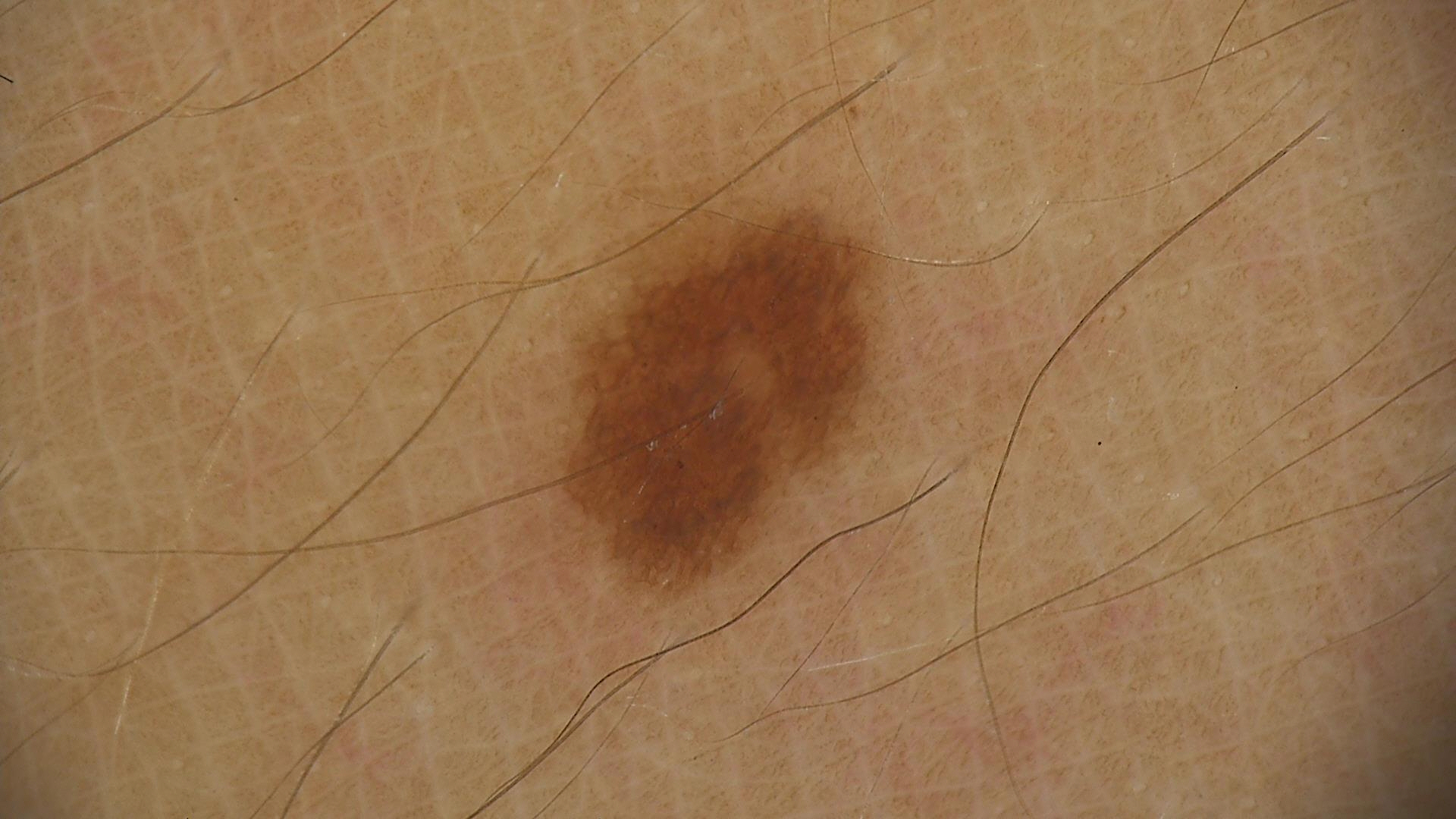Dermoscopy of a skin lesion. Labeled as a benign lesion — a dysplastic junctional nevus.